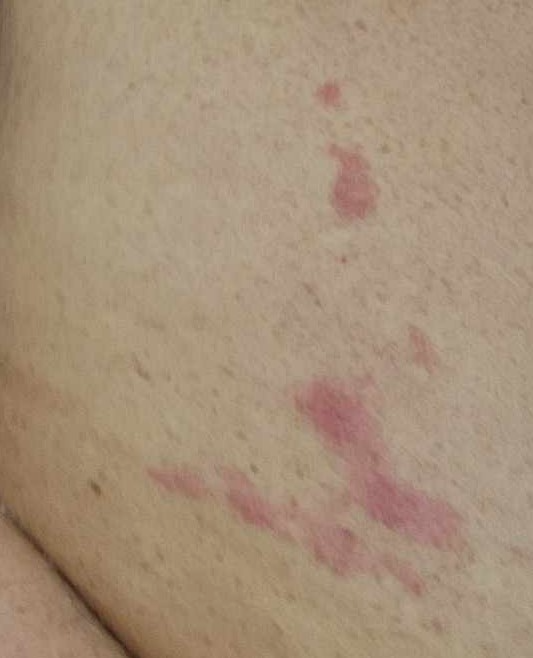The image was not sufficient for the reviewer to characterize the skin condition. Texture is reported as raised or bumpy. The photograph was taken at a distance. The affected area is the leg and front of the torso. Reported lesion symptoms include itching. Fitzpatrick skin type III; non-clinician graders estimated Monk skin tone scale 1 or 3 (two reviewer pools disagreed).